The subject is a female aged 18–29; the photograph was taken at a distance; located on the arm.
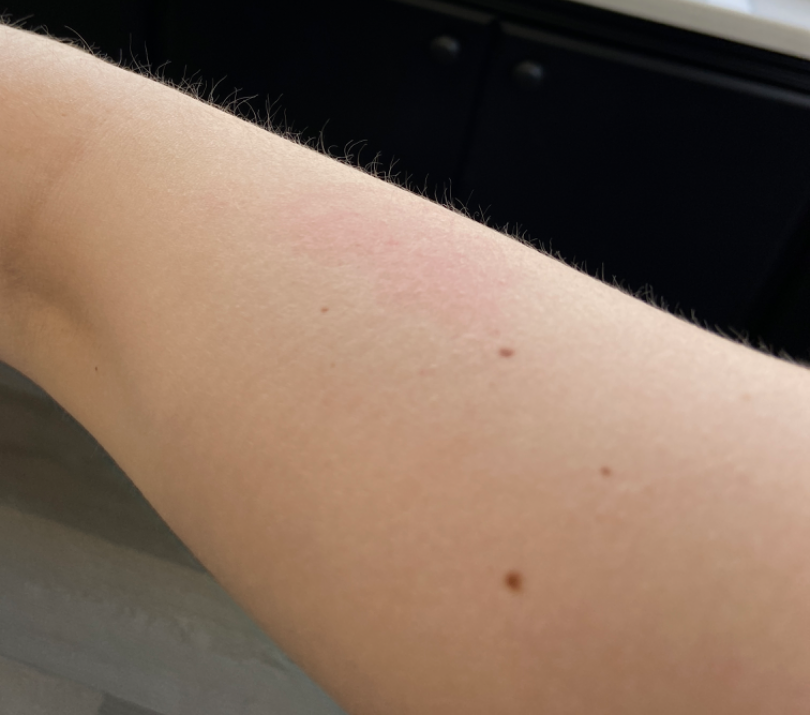{"differential": {"tied_lead": ["Eczema", "Acute dermatitis, NOS"], "considered": ["Allergic Contact Dermatitis"]}}